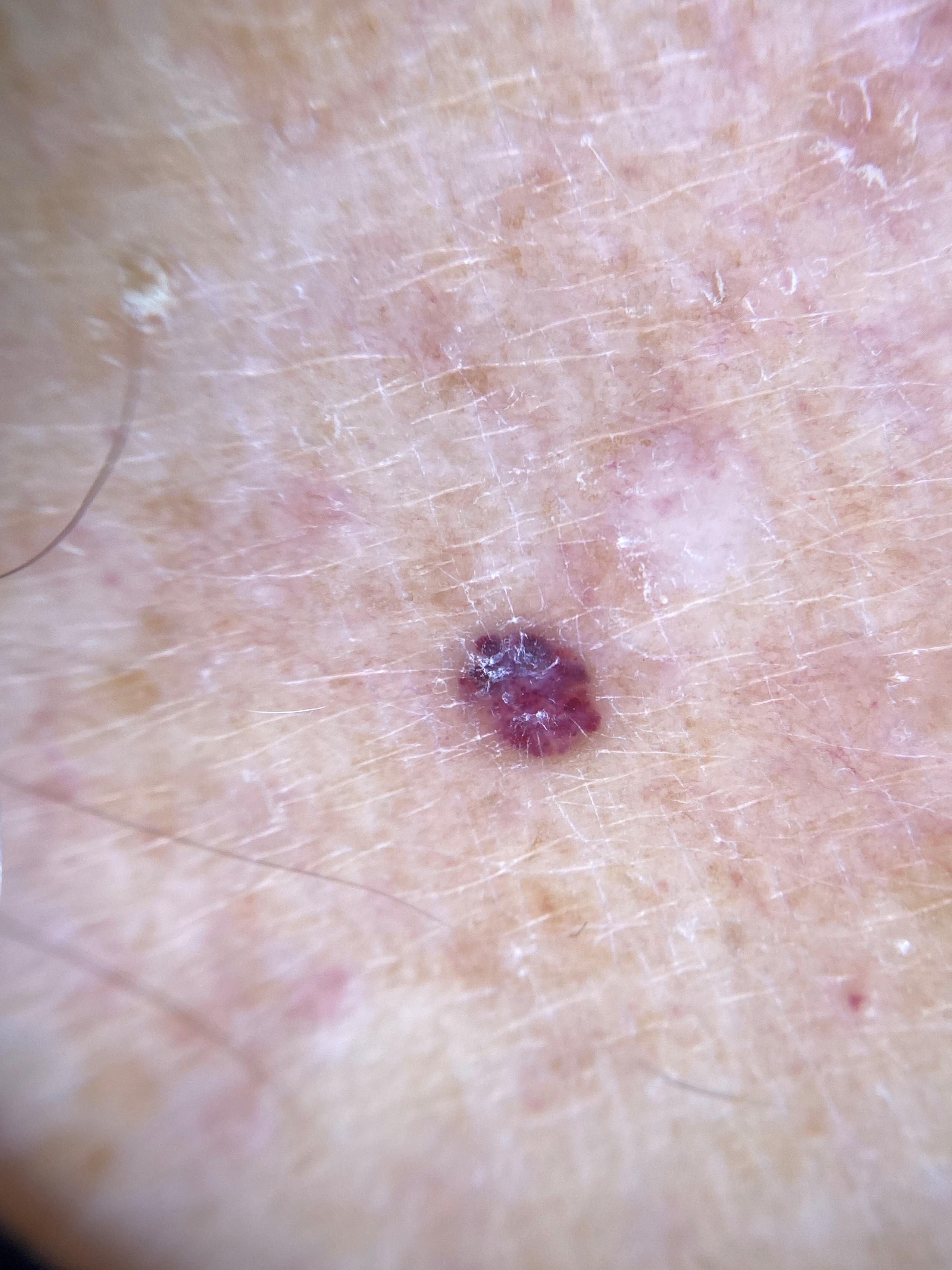{"patient": {"age_approx": 70, "sex": "male"}, "skin_type": "II", "melanoma_history": {"family_hx_melanoma": true}, "image": "dermatoscopic image", "lesion_location": {"region": "a lower extremity"}, "diagnosis": {"name": "vascular lesion", "malignancy": "benign", "confirmation": "expert clinical impression"}}